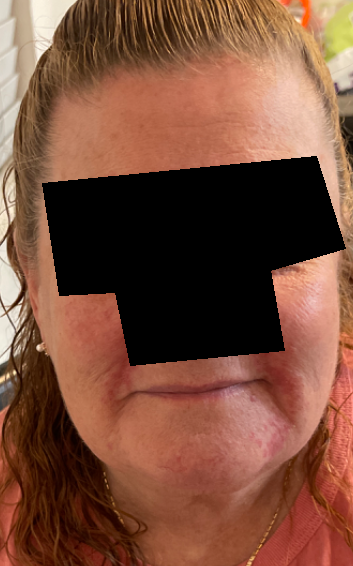Clinical context: The photo was captured at a distance. Assessment: One reviewing dermatologist: the leading consideration is Perioral Dermatitis; also raised was Rosacea.